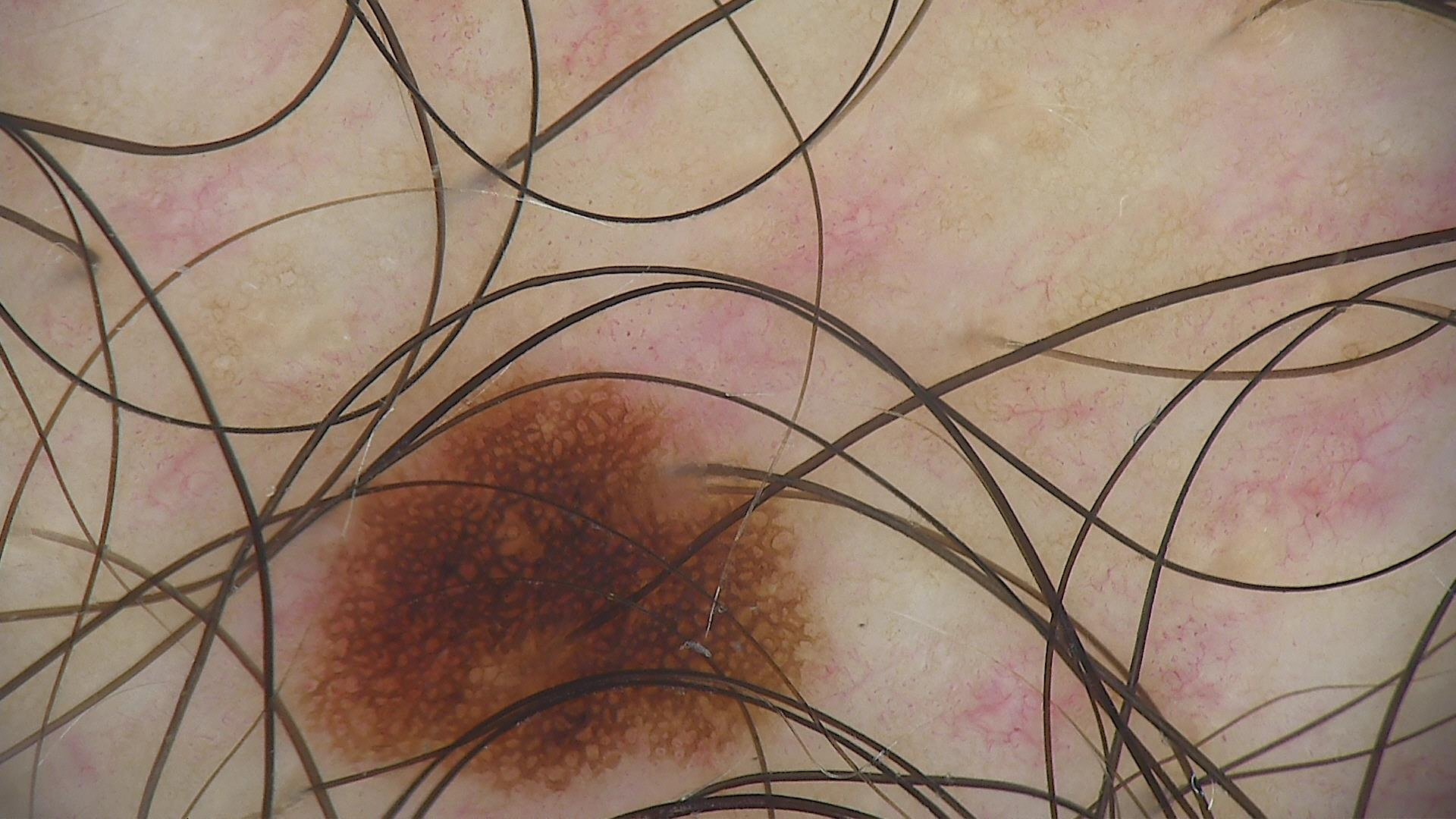A skin lesion imaged with a dermatoscope. Consistent with a dysplastic junctional nevus.